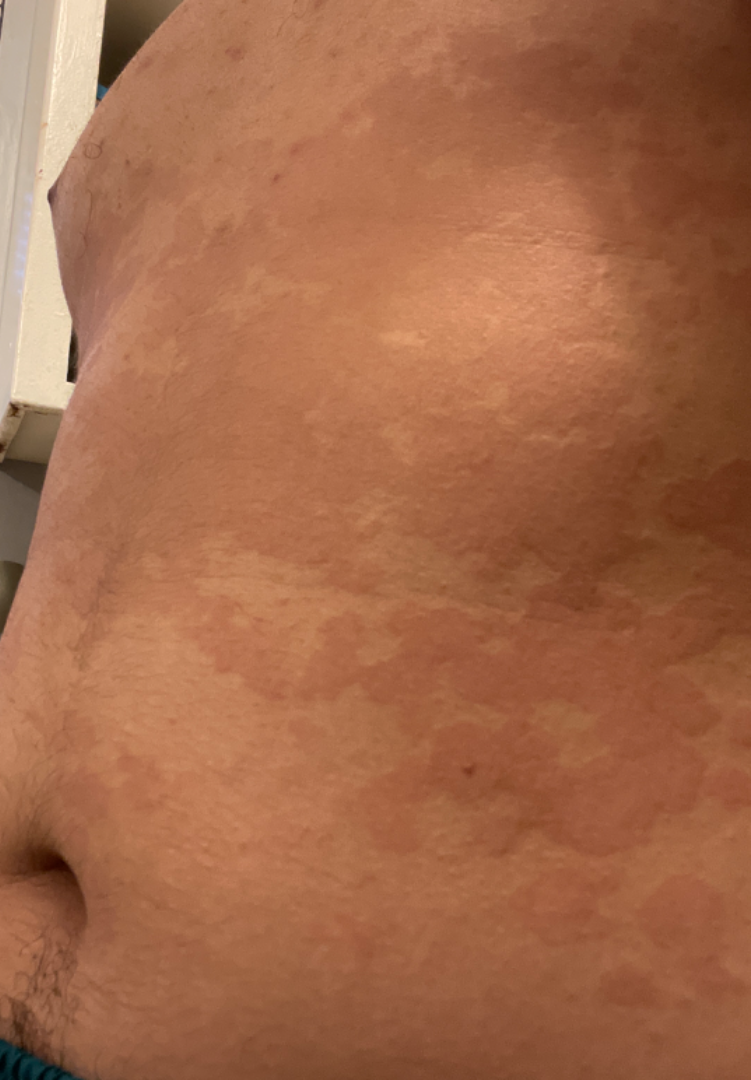Q: What is the framing?
A: close-up
Q: What symptoms does the patient report?
A: none reported
Q: Anatomic location?
A: front of the torso and back of the torso
Q: Who is the patient?
A: male, age 18–29
Q: When did this start?
A: one to three months
Q: What conditions are considered?
A: Tinea Versicolor (0.46); Urticaria (0.35); Pityriasis rubra pilaris (0.10); Psoriasis (0.10)